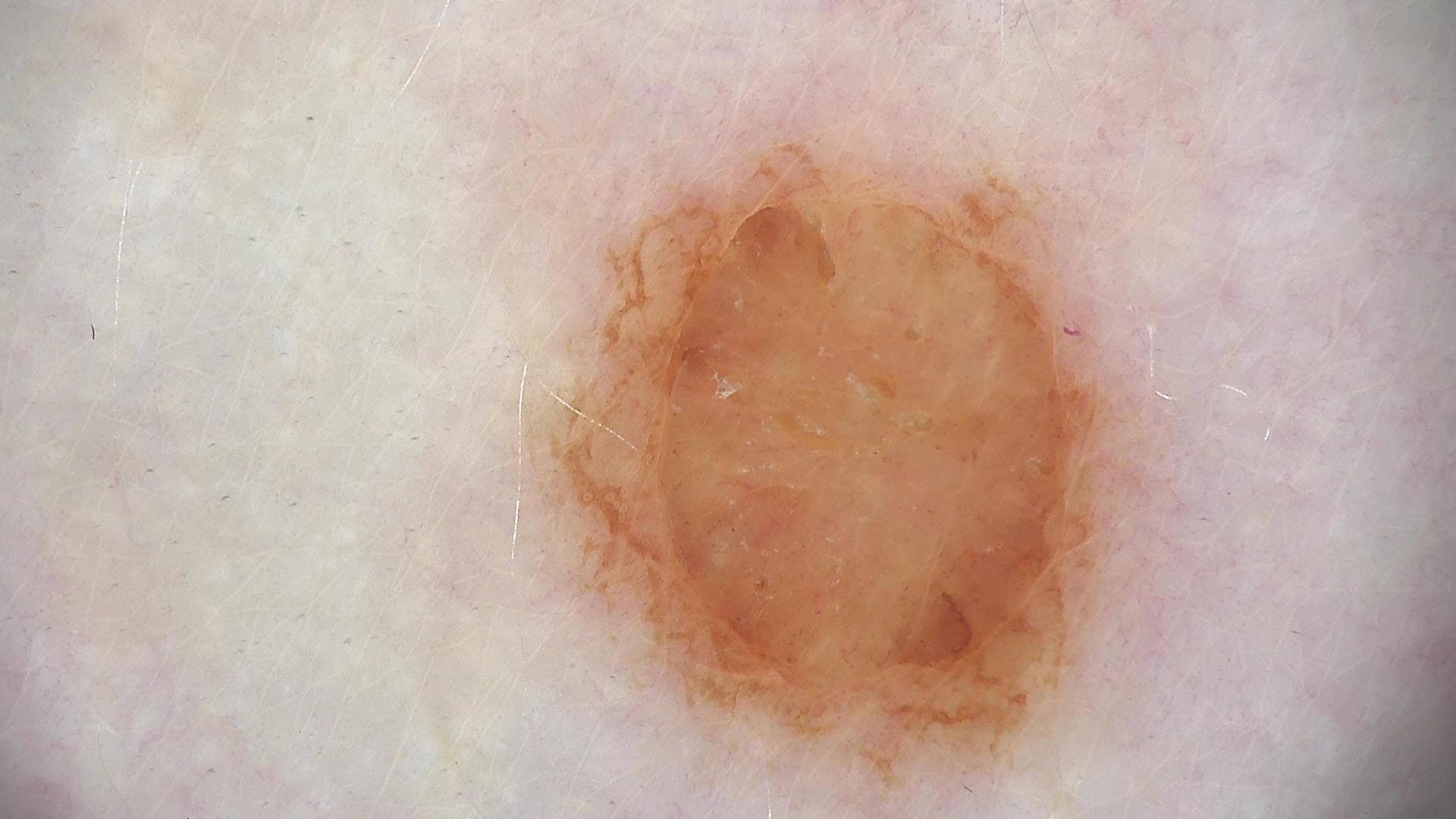diagnostic label: dermal nevus (expert consensus).